The contributor is male · the lesion is described as fluid-filled, raised or bumpy and flat · the photograph is a close-up of the affected area · symptoms reported: bothersome appearance · the lesion involves the head or neck: 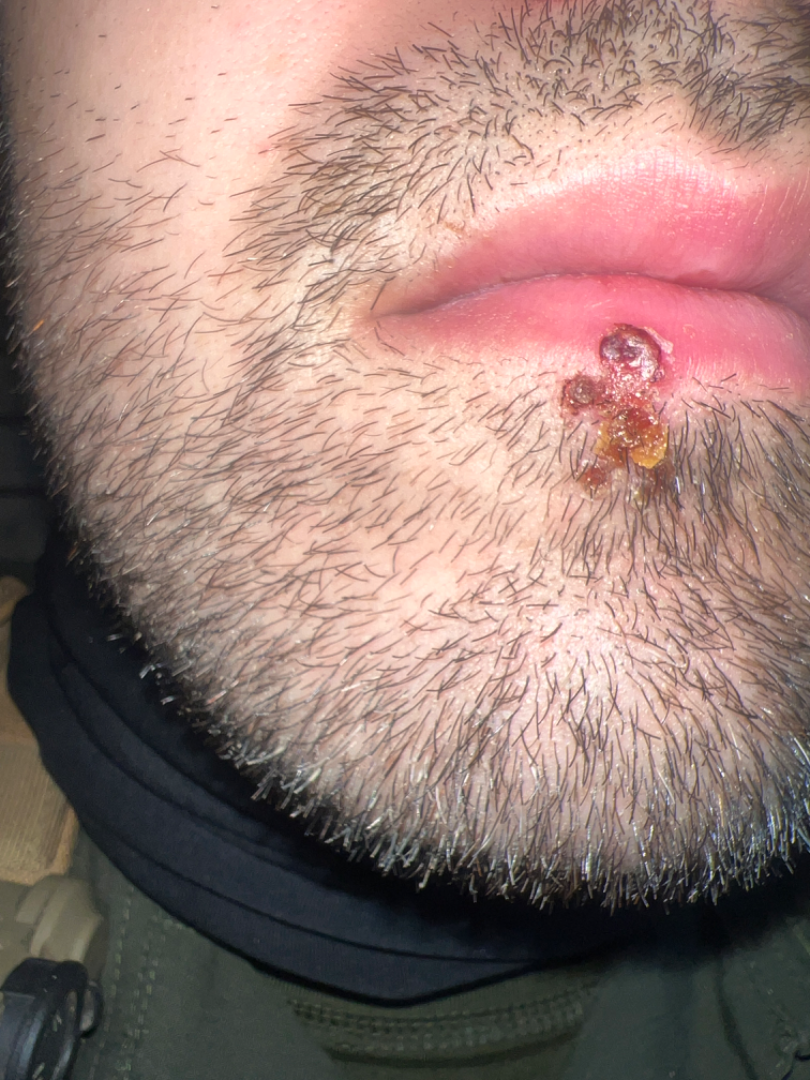assessment = ungradable on photographic review